The contributor notes darkening; no relevant systemic symptoms; the lesion is described as raised or bumpy; close-up view; the contributor is a female aged 60–69; located on the back of the hand:
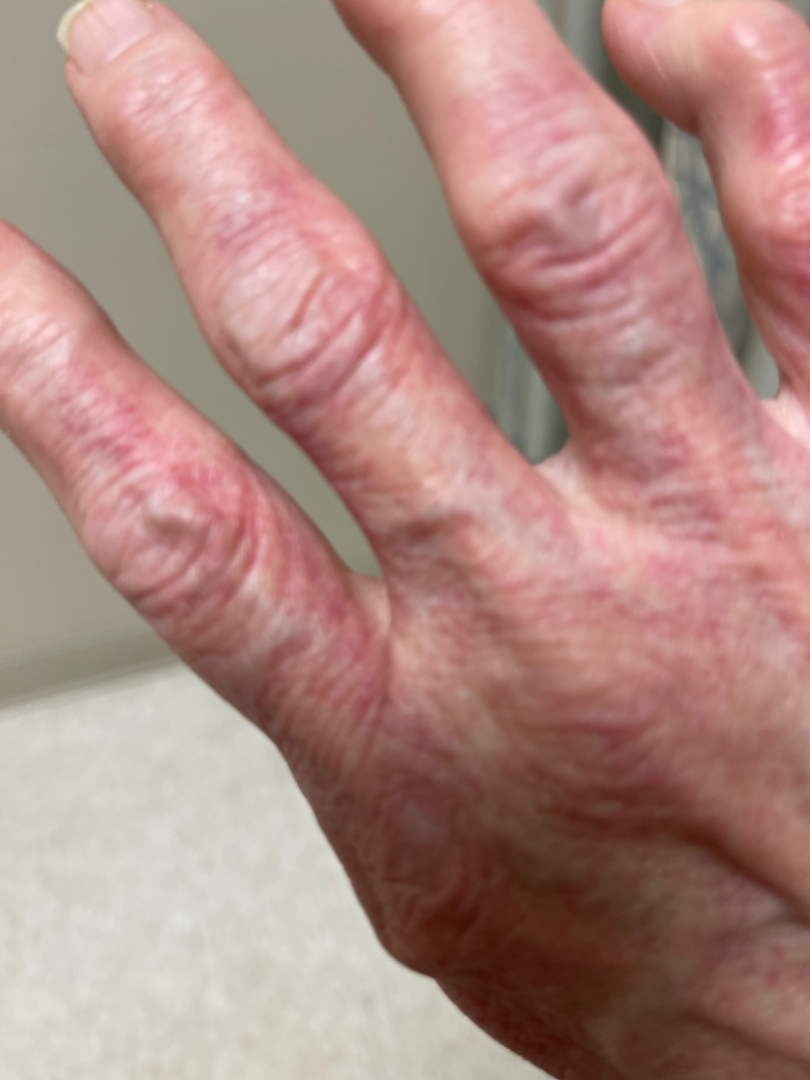| feature | finding |
|---|---|
| assessment | not assessable |